A dermatoscopic image of a skin lesion.
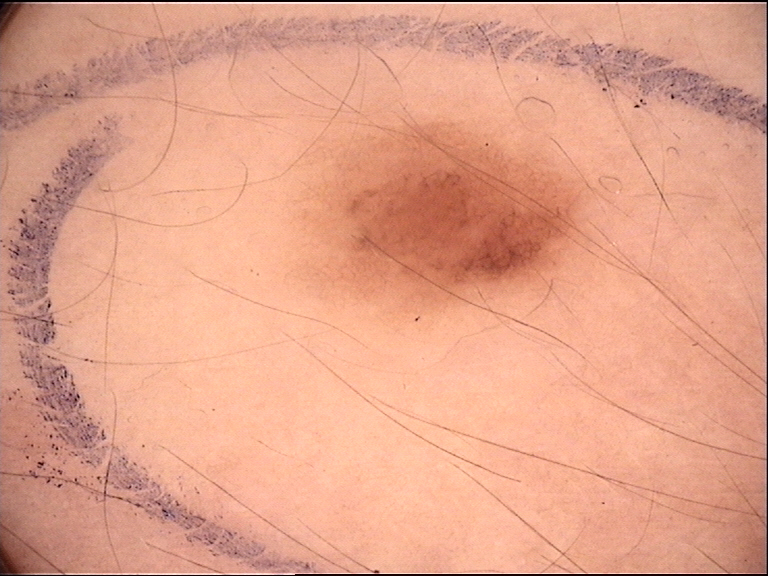Conclusion: The diagnosis was a dysplastic junctional nevus.